A dermatoscopic image of a skin lesion:
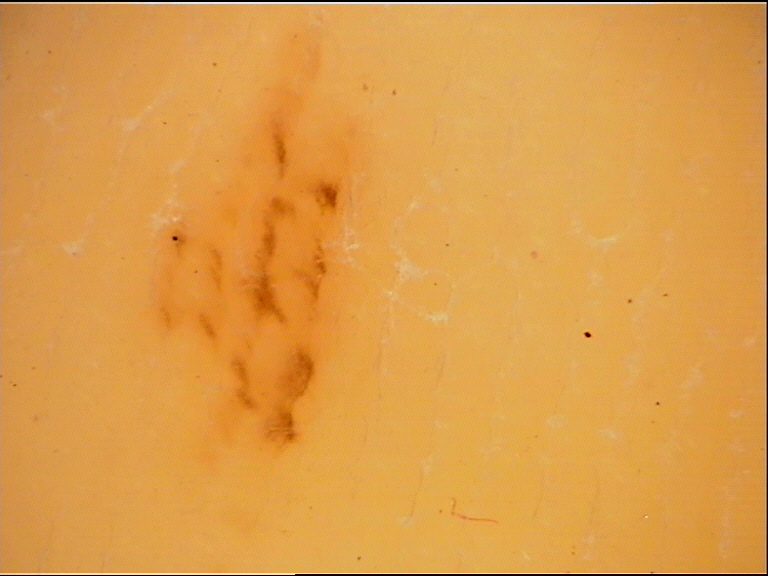label: acral junctional nevus (expert consensus).